A skin lesion imaged with a dermatoscope.
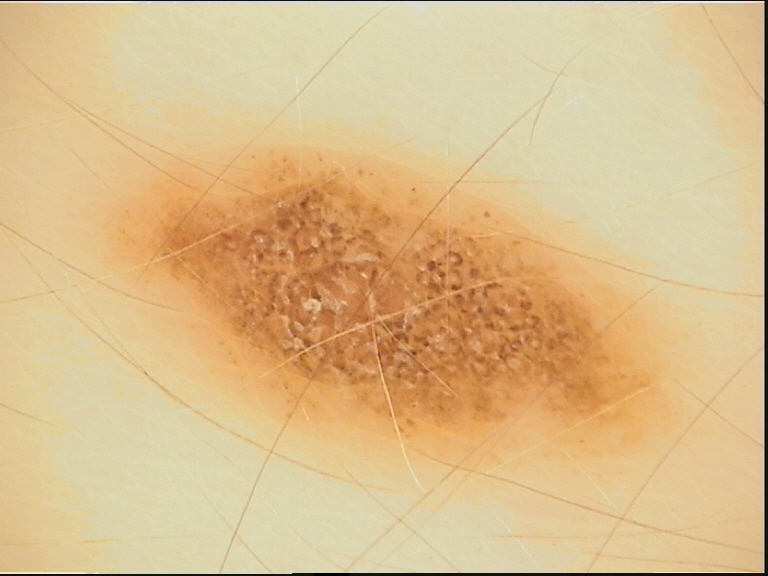Consistent with a banal lesion — a compound nevus.